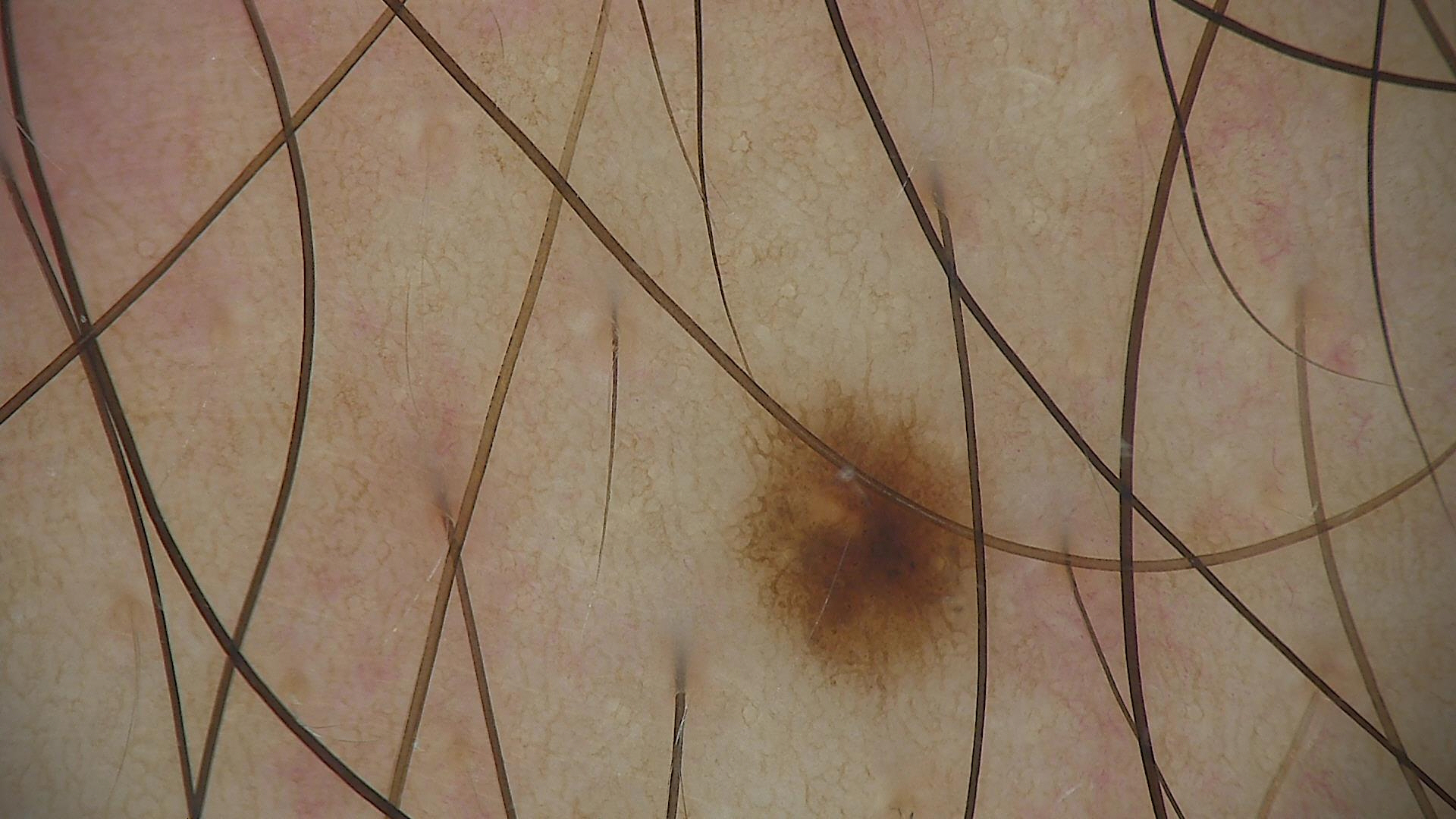<lesion>
  <diagnosis>
    <name>dysplastic junctional nevus</name>
    <code>jd</code>
    <malignancy>benign</malignancy>
    <super_class>melanocytic</super_class>
    <confirmation>expert consensus</confirmation>
  </diagnosis>
</lesion>